A skin lesion imaged with a dermatoscope — 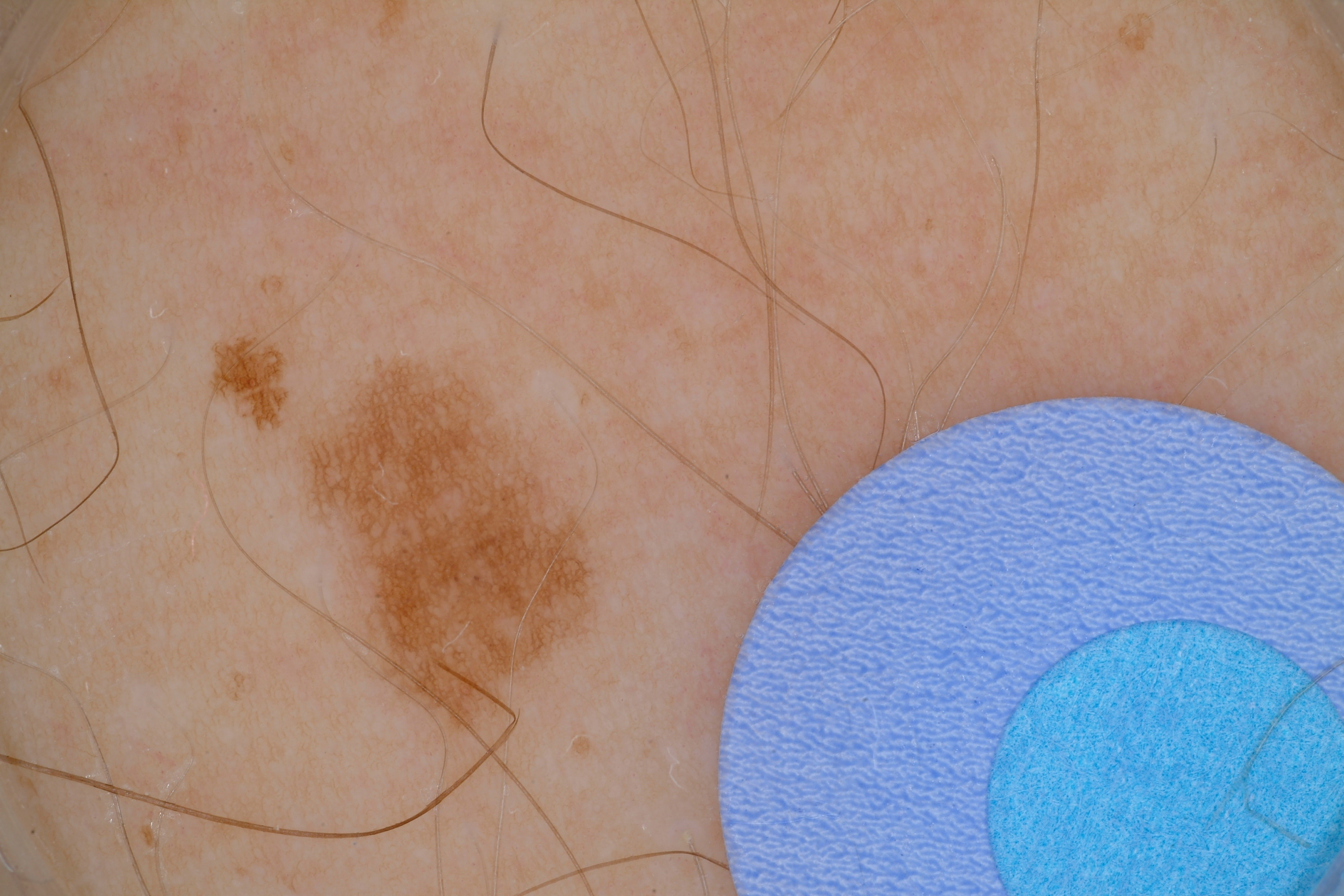The lesion covers approximately 7% of the dermoscopic field.
On dermoscopy, the lesion shows neither globules nor streaks.
The visible lesion spans left=273, top=339, right=611, bottom=739.
Diagnosed as a benign lesion.